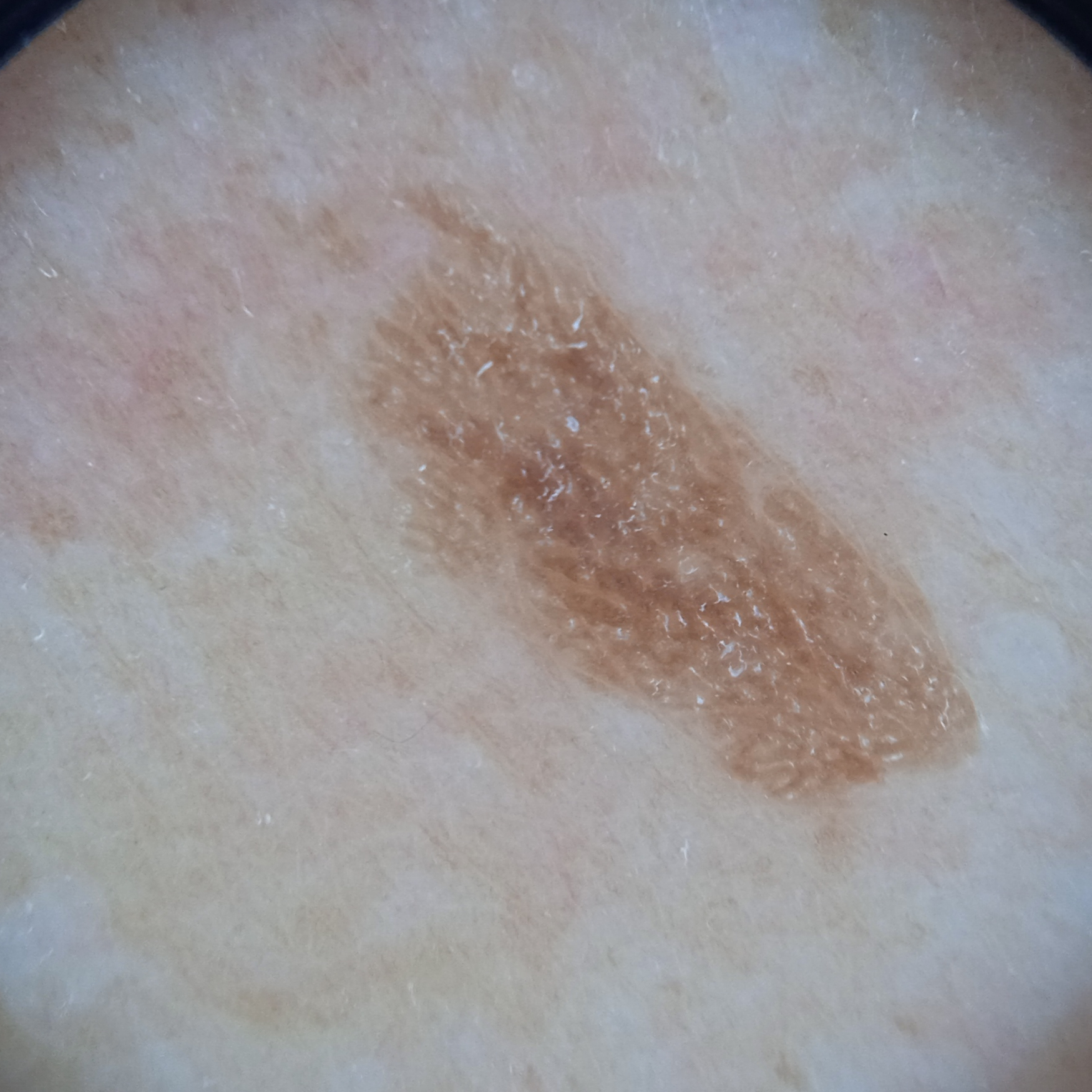A moderate number of moles by the patient's own estimate. A dermoscopic image of a skin lesion. Imaged for a research study, with no referral diagnosis recorded. The patient says their skin tans without first burning. The lesion is located on the back. The lesion measures approximately 8.4 mm. Dermatologist review favored a seborrheic keratosis.